The lesion involves the leg, an image taken at an angle, the subject is a male aged 30–39, reported duration is less than one week, the patient indicates bothersome appearance:
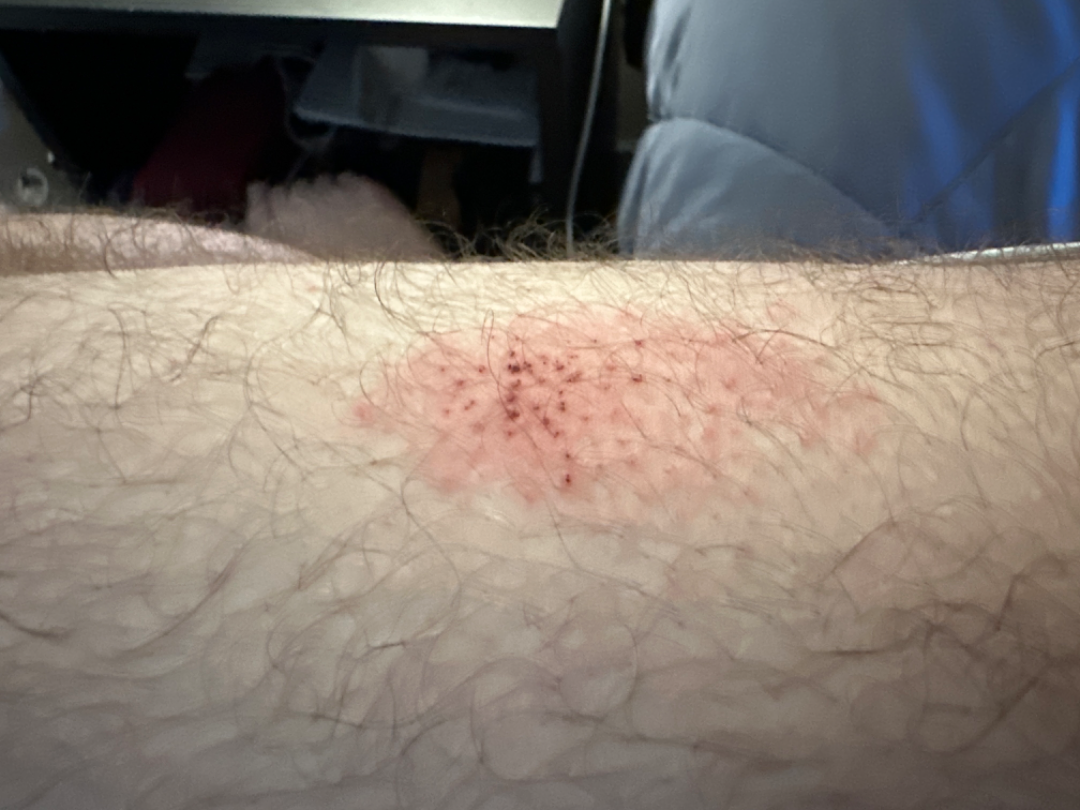Impression:
On teledermatology review: the leading impression is Abrasion, scrape, or scab; also on the differential is Eczema.